Located on the head or neck, leg and arm; the patient is 50–59, female; the photograph was taken at an angle — 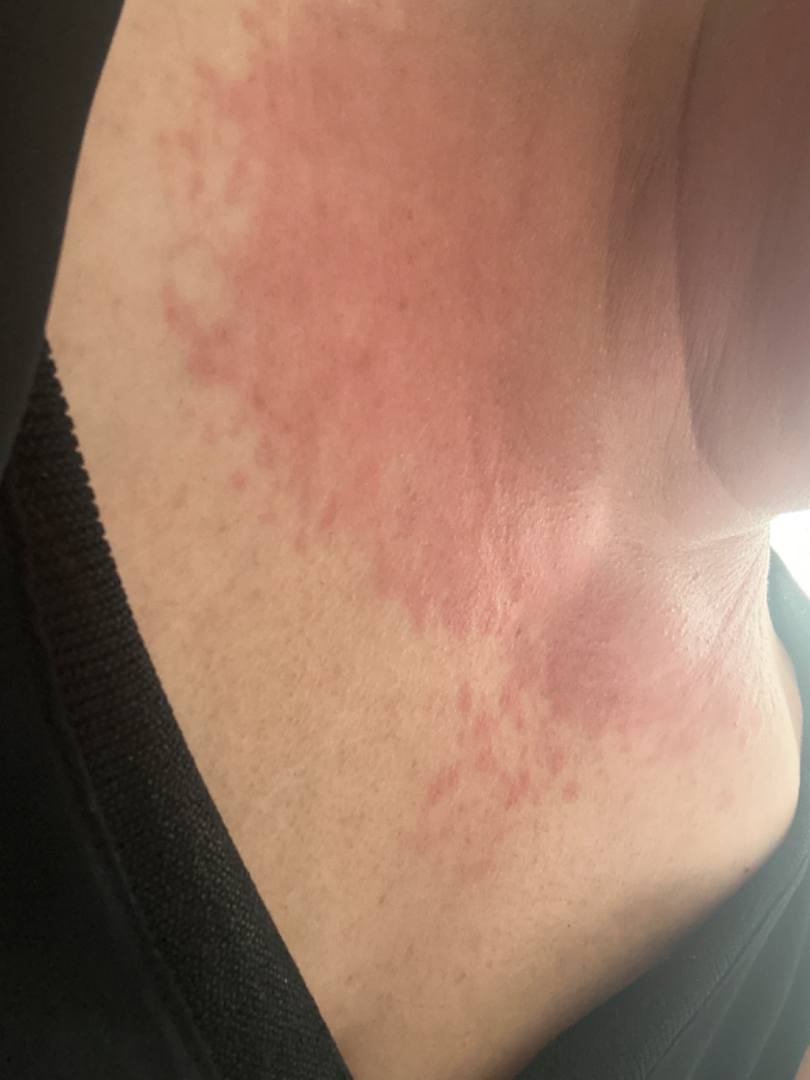Q: What is the dermatologist's impression?
A: most consistent with Cutaneous lupus; the differential also includes Dermatomyositis; also consider Allergic Contact Dermatitis